An image taken at an angle; male patient, age 18–29; the arm is involved: 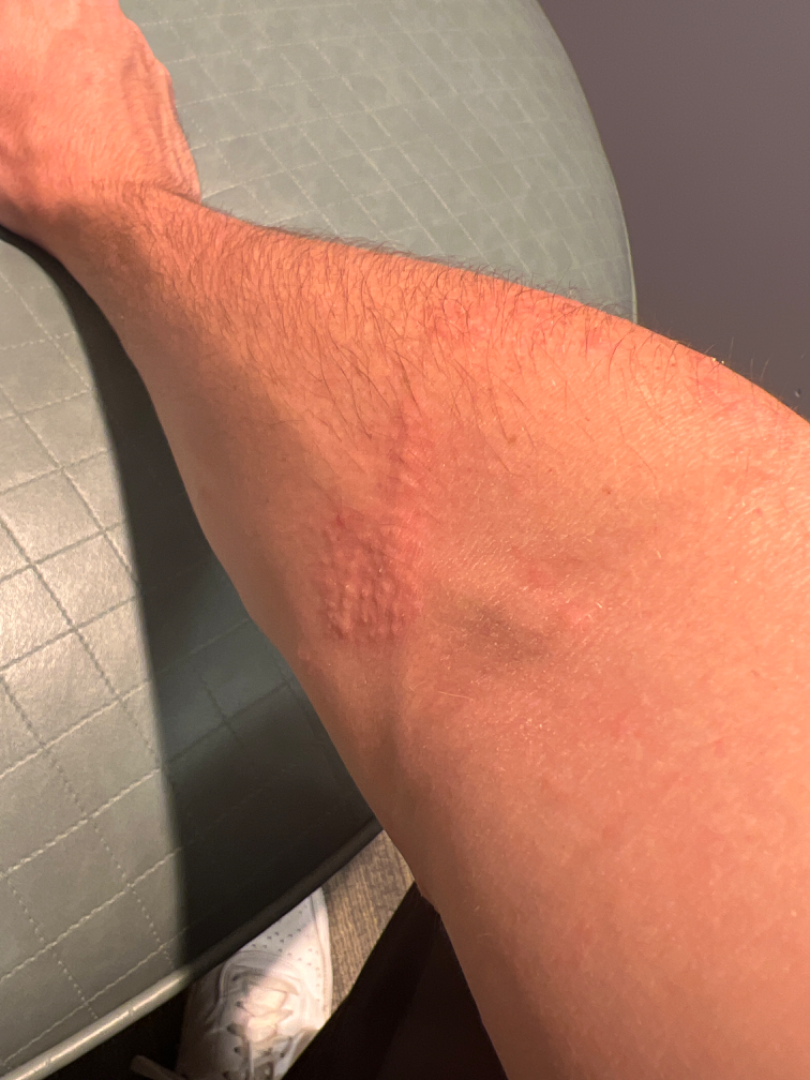Eczema (favored).